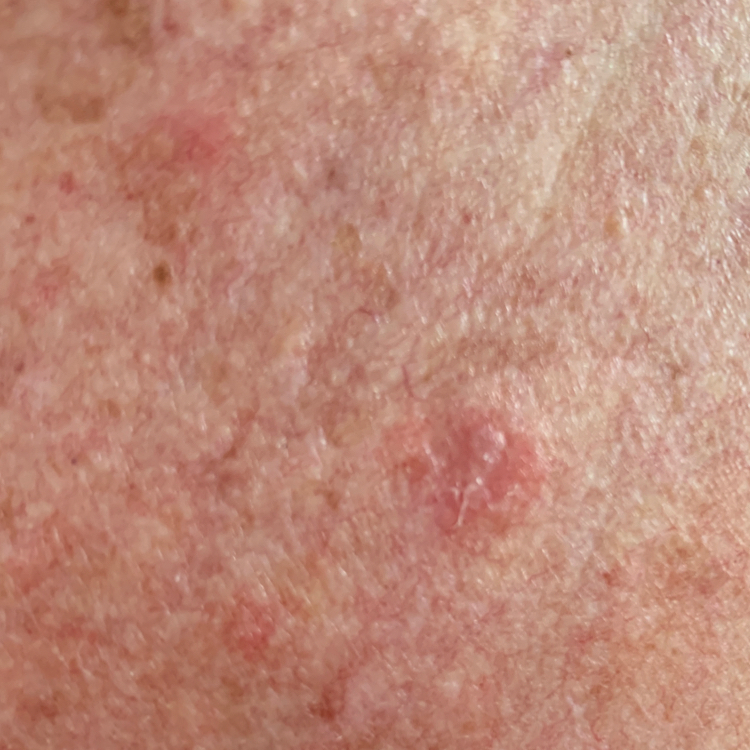diagnosis = actinic keratosis (clinical consensus).